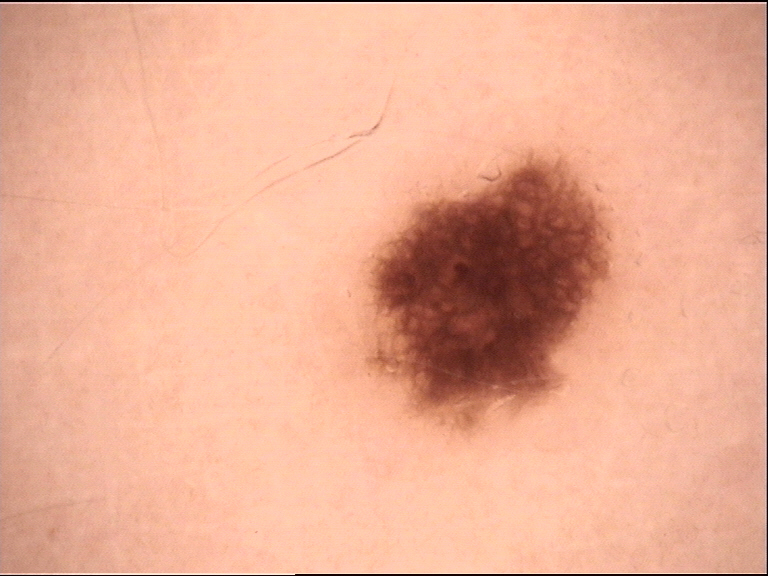image type = dermoscopy; assessment = dysplastic junctional nevus (expert consensus).